The photograph is a close-up of the affected area. Located on the head or neck, back of the torso and arm. The patient is a female aged 30–39:
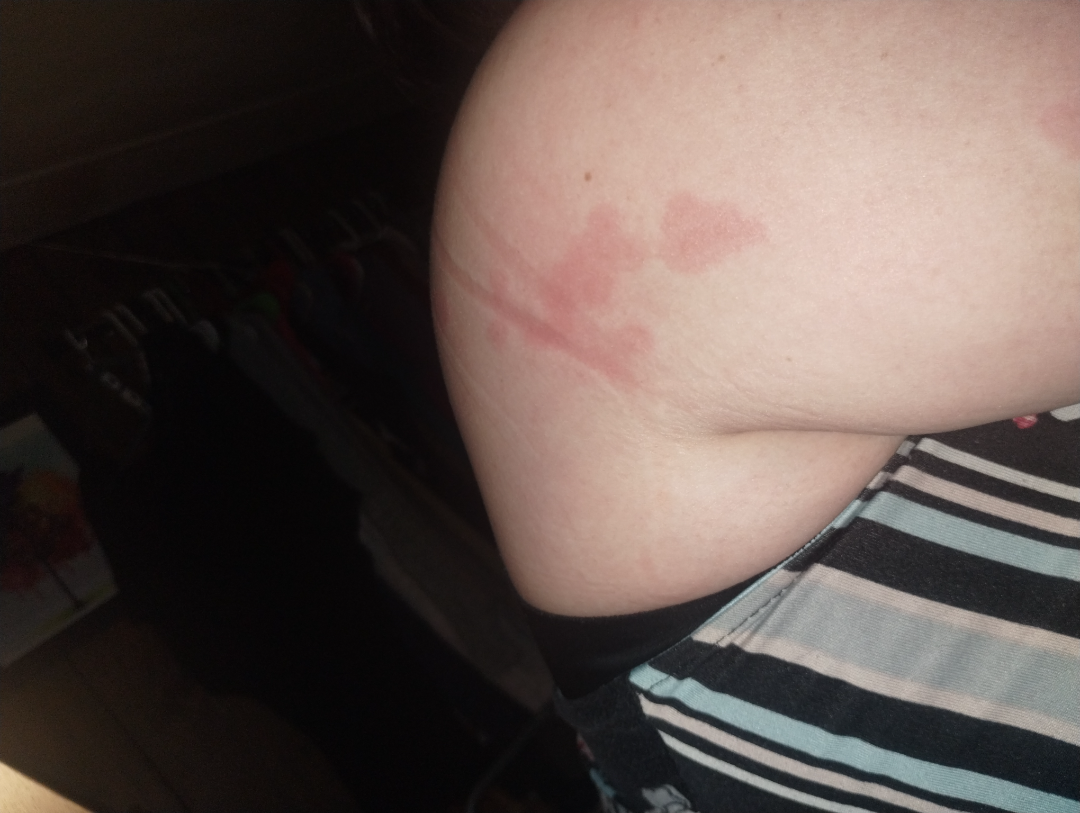Q: Could the case be diagnosed?
A: indeterminate
Q: Any systemic symptoms?
A: joint pain and fatigue
Q: Duration?
A: more than five years
Q: What symptoms does the patient report?
A: none reported
Q: Patient's own categorization?
A: a rash